Fitzpatrick III · the patient notes the condition has been present for about one day · an image taken at an angle · no constitutional symptoms were reported · the arm is involved · the contributor is 18–29, male · the patient described the issue as a rash: 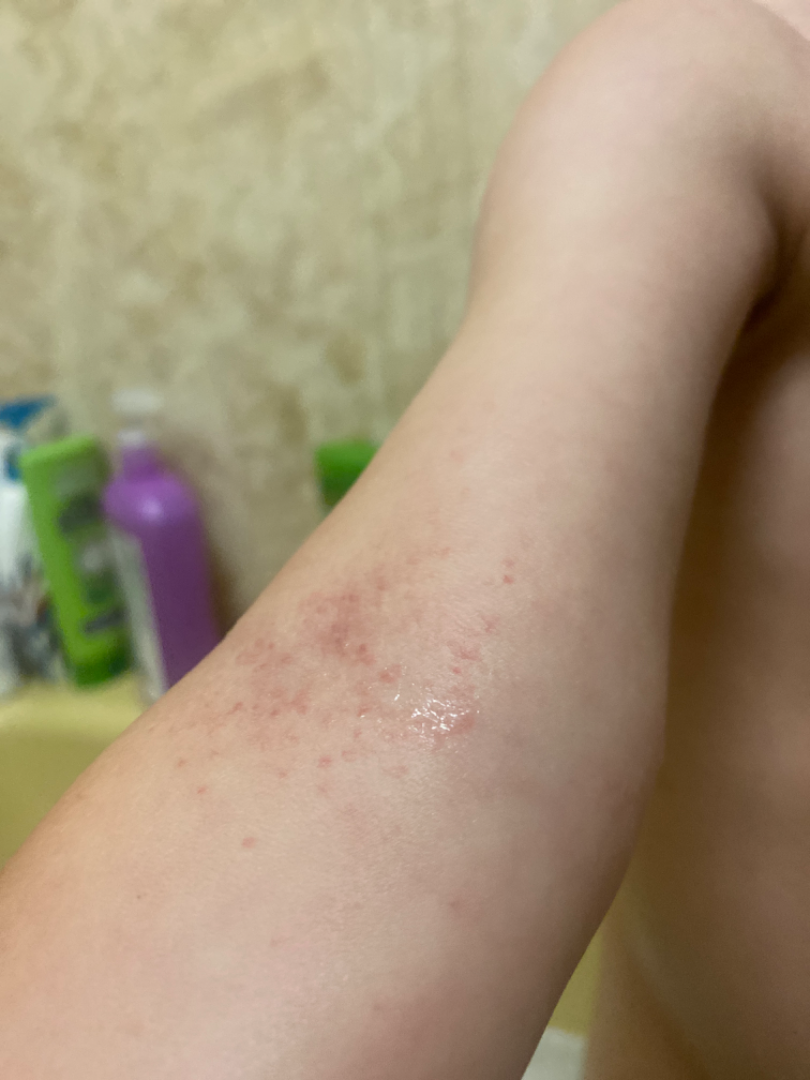Case summary:
• differential — most consistent with Eczema